The patient was assessed as FST II; a wide-field clinical photograph of a skin lesion; a female patient about 65 years old:
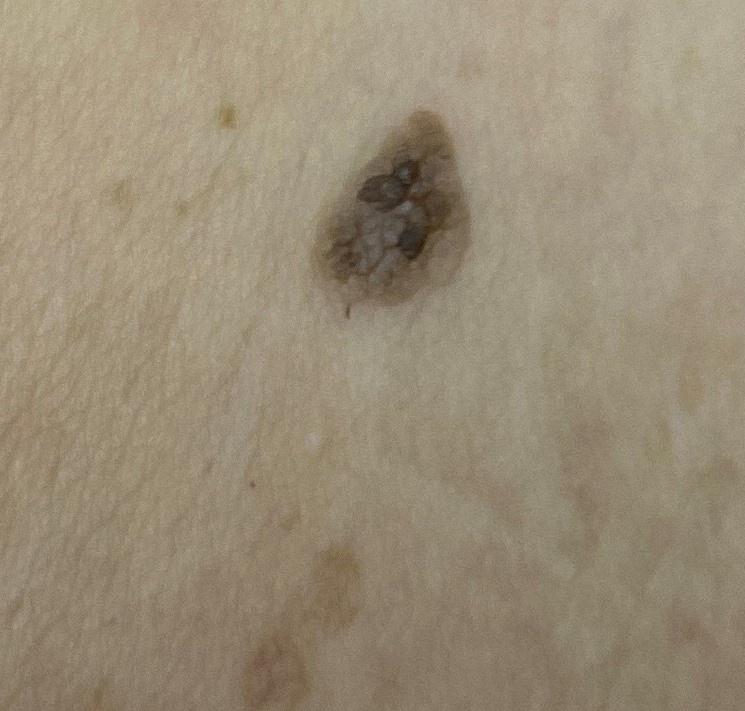| field | value |
|---|---|
| diagnostic label | Seborrheic keratosis (clinical impression) |